A dermoscopic view of a skin lesion. The subject is a female aged around 60: 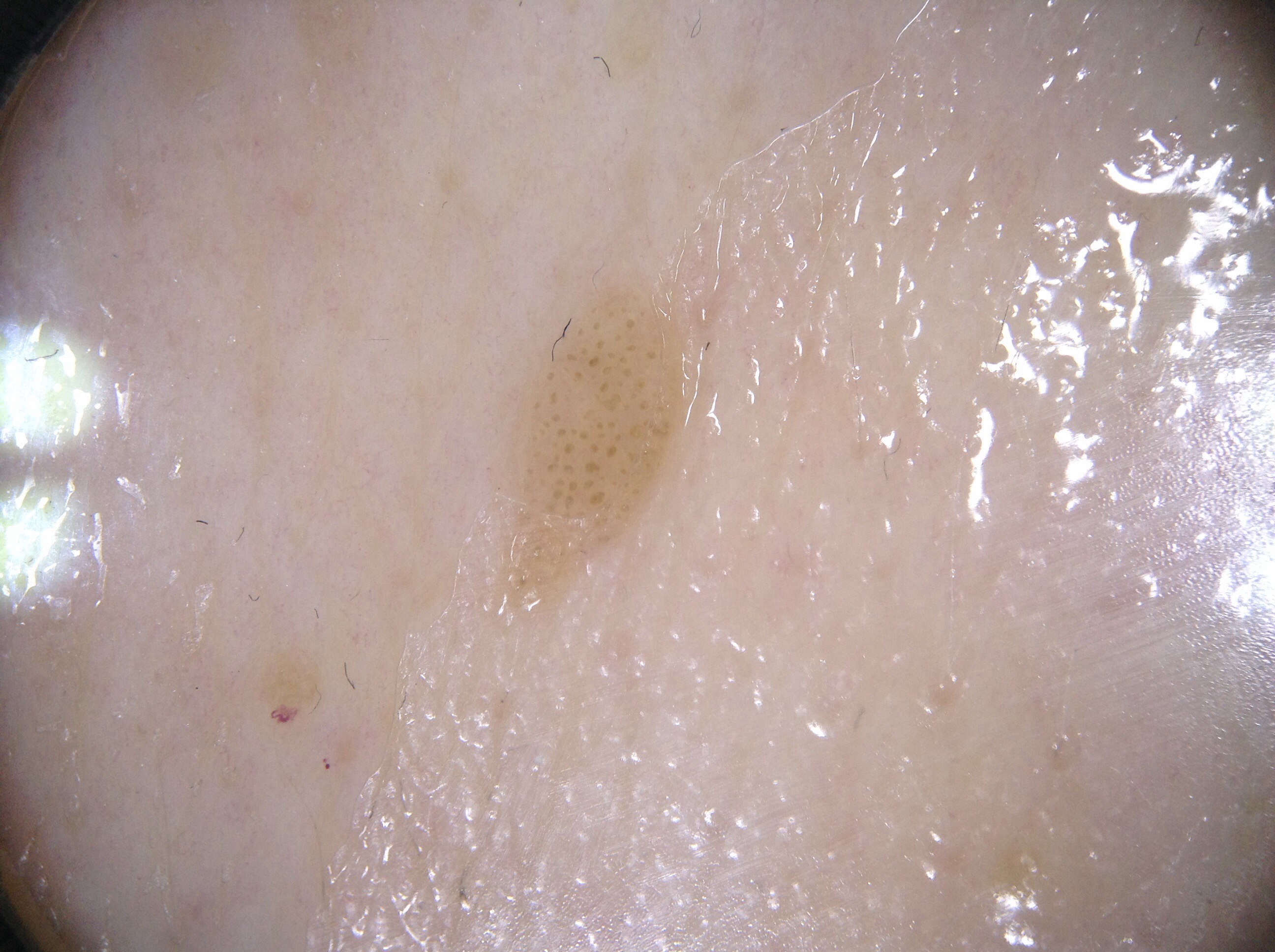absent dermoscopic findings = streaks, milia-like cysts, pigment network, and negative network; lesion bbox = x1=493, y1=271, x2=724, y2=612; lesion size = ~4% of the field; diagnostic label = a seborrheic keratosis, a benign lesion.